A patient aged 52 · a clinical photograph showing a skin lesion.
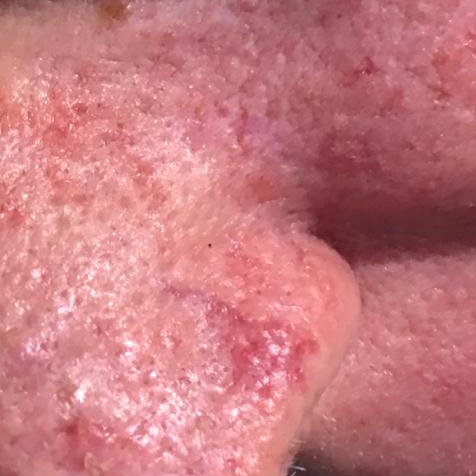The lesion is located on the face. The patient describes that the lesion itches, but is not elevated. Diagnosed by dermatologist consensus as a lesion with uncertain malignant potential — an actinic keratosis.